A dermoscopic close-up of a skin lesion: 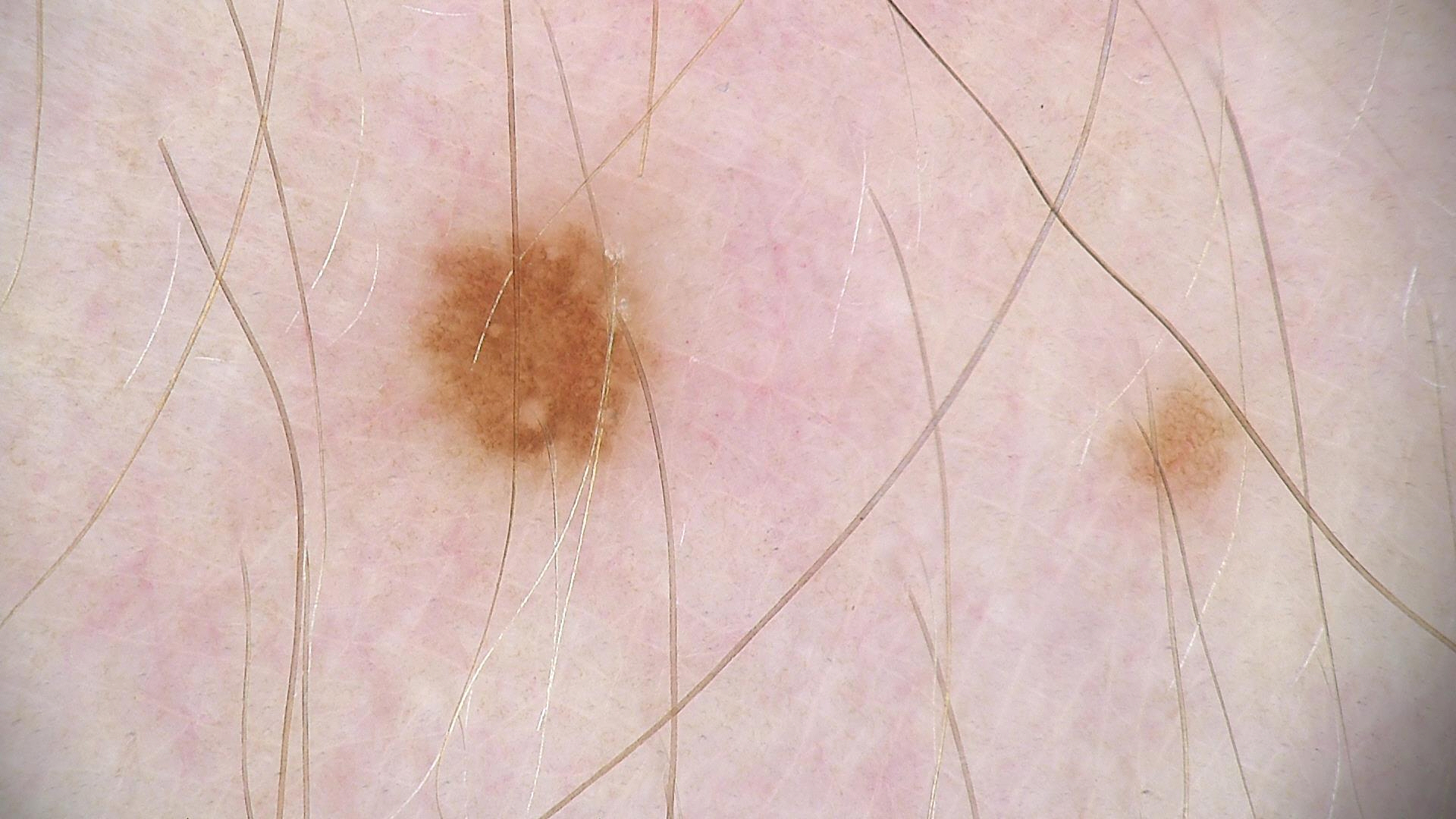  diagnosis:
    name: dysplastic junctional nevus
    code: jd
    malignancy: benign
    super_class: melanocytic
    confirmation: expert consensus